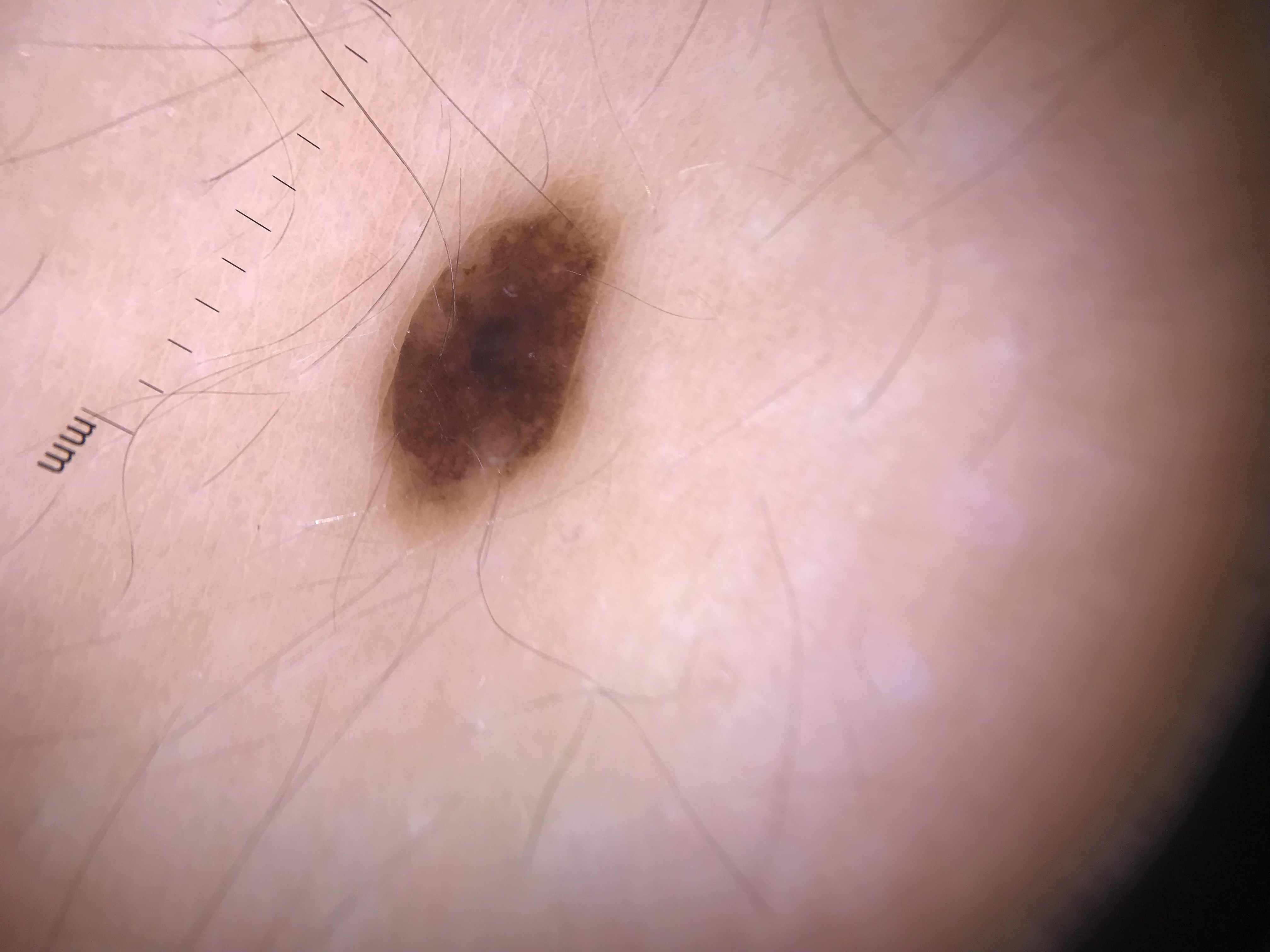Case: Dermoscopy of a skin lesion. Impression: The diagnosis was a banal lesion — a compound nevus.